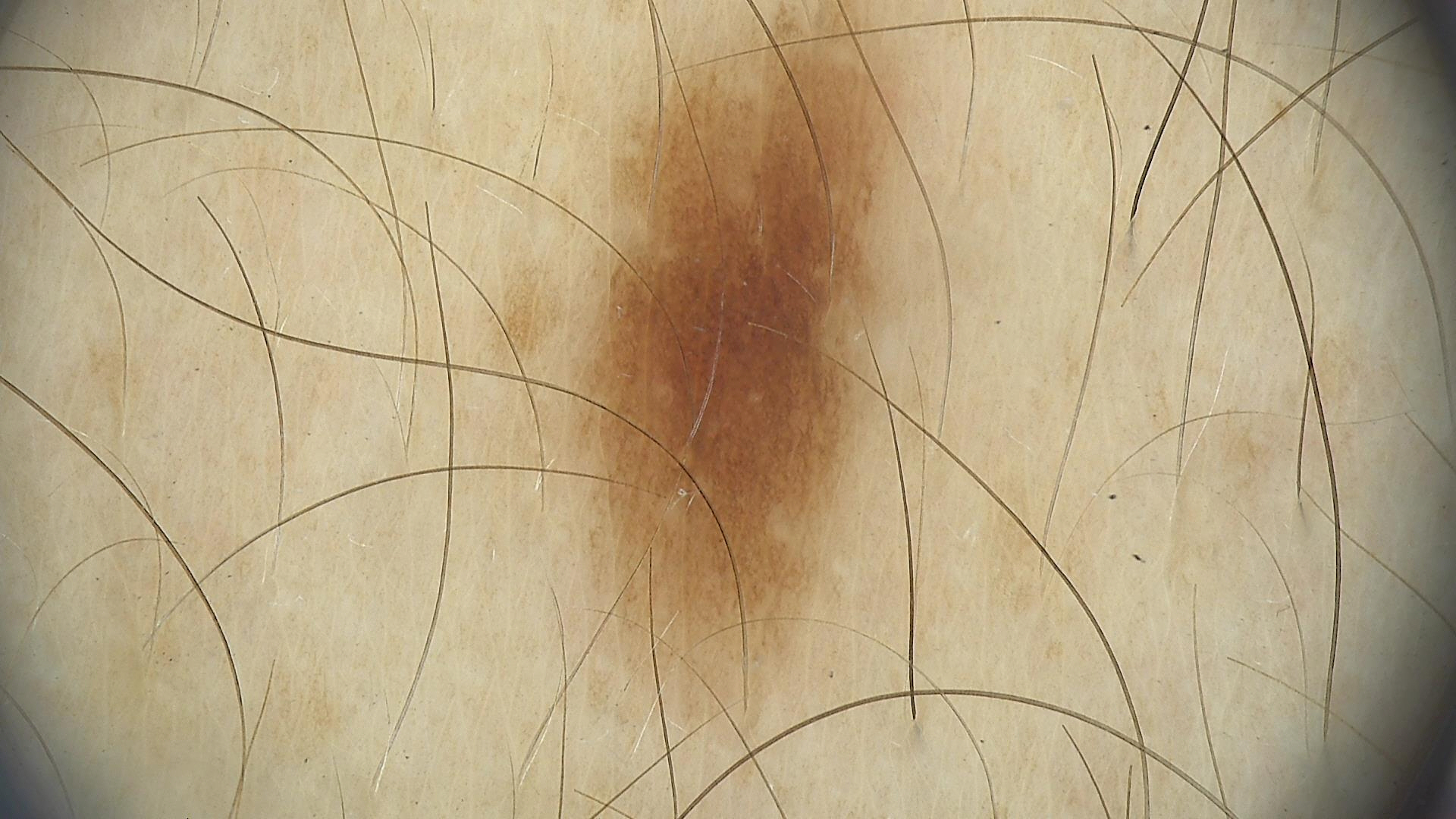Q: What is the imaging modality?
A: dermatoscopy
Q: What is the diagnosis?
A: dysplastic junctional nevus (expert consensus)